The contributor is female · this is a close-up image · located on the leg:
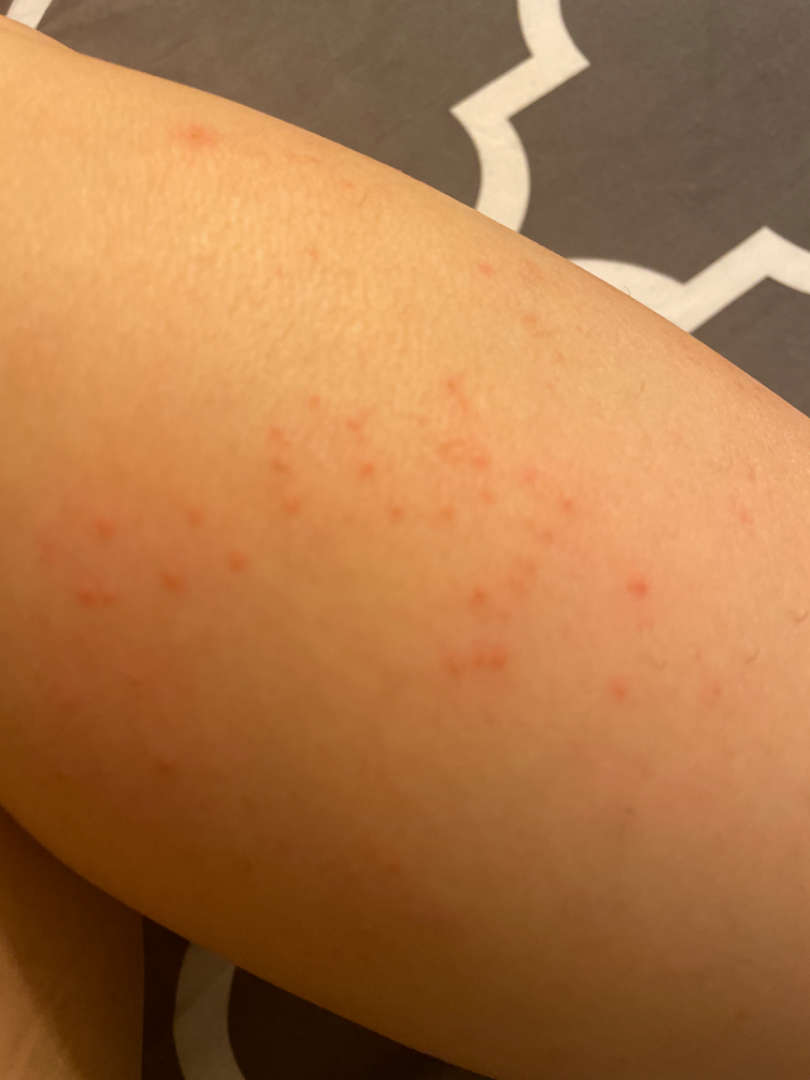The lesion is associated with itching. The patient considered this a rash. The lesion is described as rough or flaky. The condition has been present for one to four weeks. On teledermatology review, Folliculitis (favored); Insect Bite (possible); Allergic Contact Dermatitis (possible).